A skin lesion imaged with a dermatoscope:
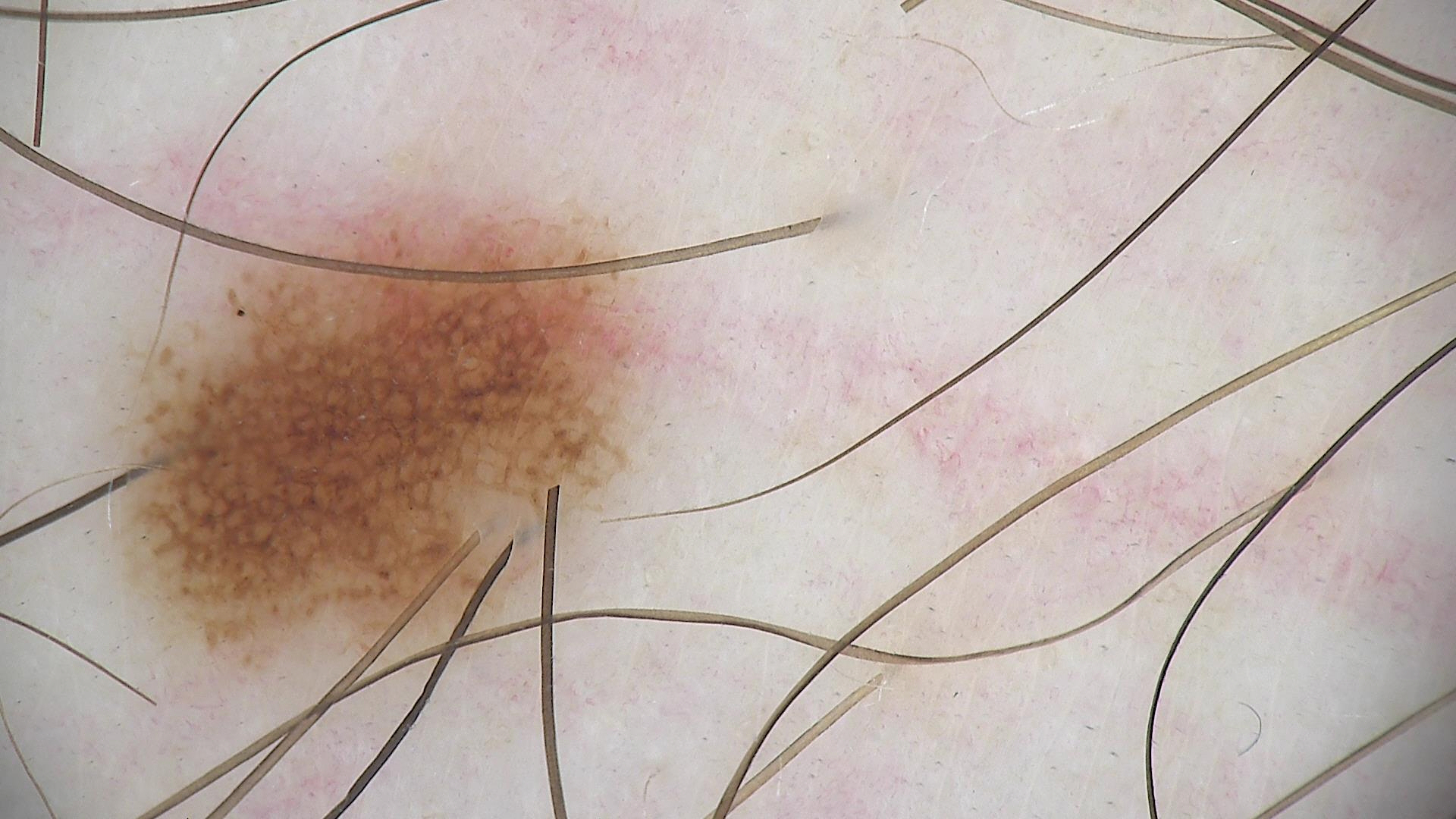<lesion>
  <diagnosis>
    <name>dysplastic junctional nevus</name>
    <code>jd</code>
    <malignancy>benign</malignancy>
    <super_class>melanocytic</super_class>
    <confirmation>expert consensus</confirmation>
  </diagnosis>
</lesion>